An image taken at an angle · the lesion is described as rough or flaky · the arm is involved · self-categorized by the patient as a rash · the lesion is associated with itching · Fitzpatrick skin type II · the patient is 18–29, female: 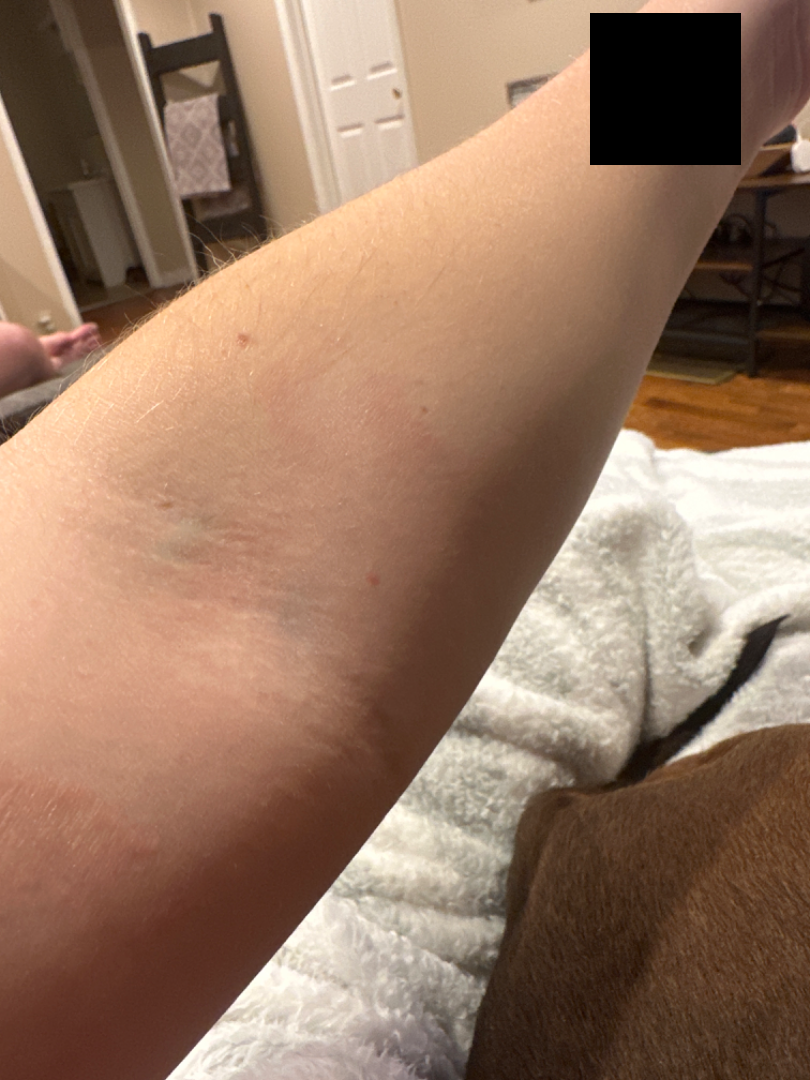{
  "differential": {
    "leading": [
      "Lichen planus/lichenoid eruption"
    ],
    "considered": [
      "Parapsoriasis",
      "Eczema"
    ]
  }
}